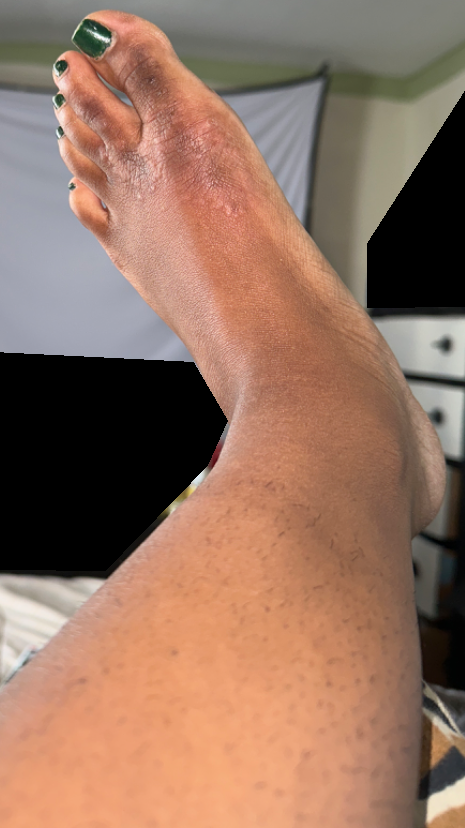The condition could not be reliably identified from the image.
The subject is a female aged 18–29.
The lesion is associated with itching, bothersome appearance, darkening, pain and burning.
The patient indicates the condition has been present for more than five years.
Fitzpatrick IV; lay reviewers estimated MST 5 or 7 (two reviewer pools disagreed).
Texture is reported as raised or bumpy, fluid-filled and flat.
Located on the top or side of the foot and back of the hand.
This image was taken at a distance.